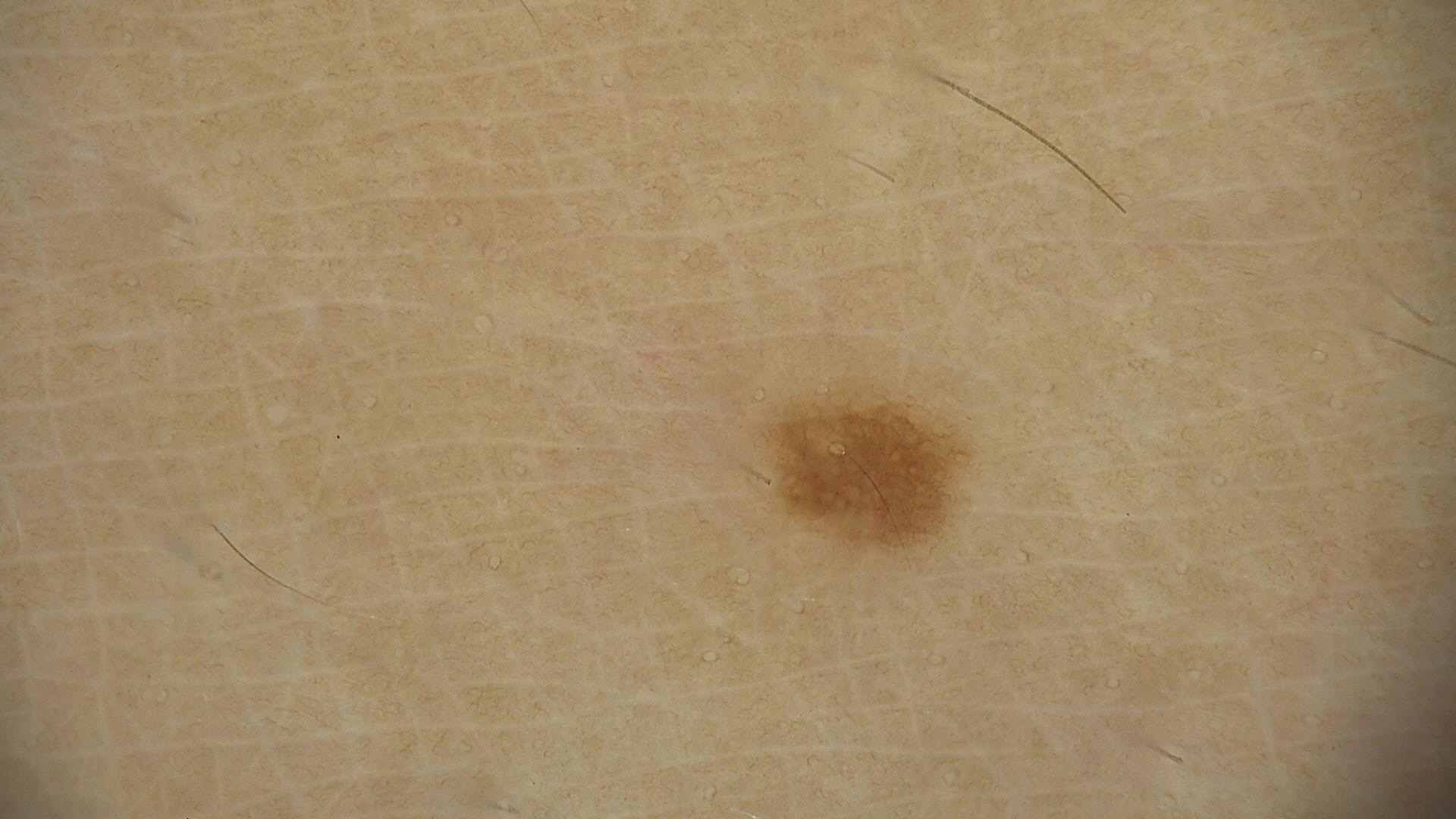Q: What is the imaging modality?
A: dermoscopy
Q: What is this lesion?
A: dysplastic junctional nevus (expert consensus)